The lesion involves the head or neck · female patient, age 50–59 · an image taken at a distance: 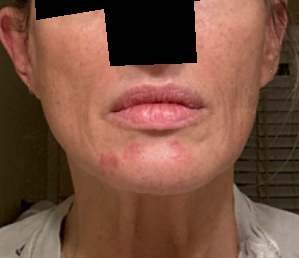  patient_category: a rash
  symptoms: bothersome appearance
  duration: one to four weeks
  skin_tone:
    fitzpatrick: II
    monk_skin_tone:
      - 2
      - 3
  texture: raised or bumpy
  differential:
    leading:
      - Perioral Dermatitis